An image taken at an angle, the lesion involves the leg.
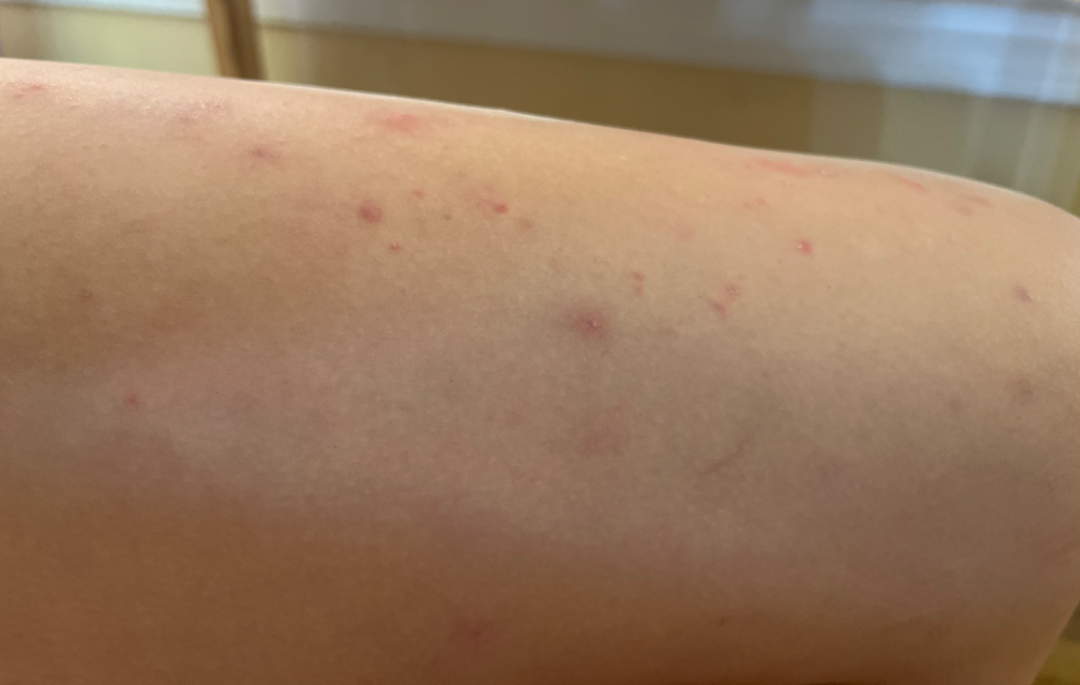Present for one to three months. In keeping with Folliculitis.